A dermoscopic close-up of a skin lesion.
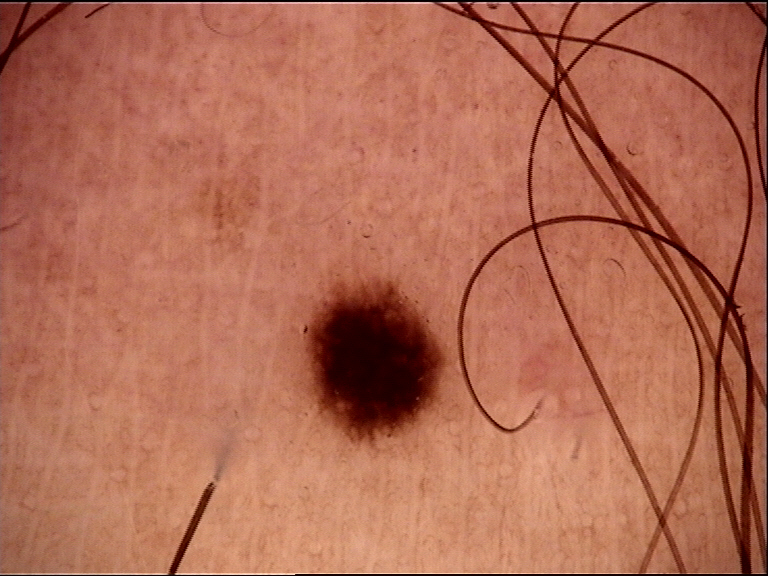{
  "diagnosis": {
    "name": "dysplastic junctional nevus",
    "code": "jd",
    "malignancy": "benign",
    "super_class": "melanocytic",
    "confirmation": "expert consensus"
  }
}